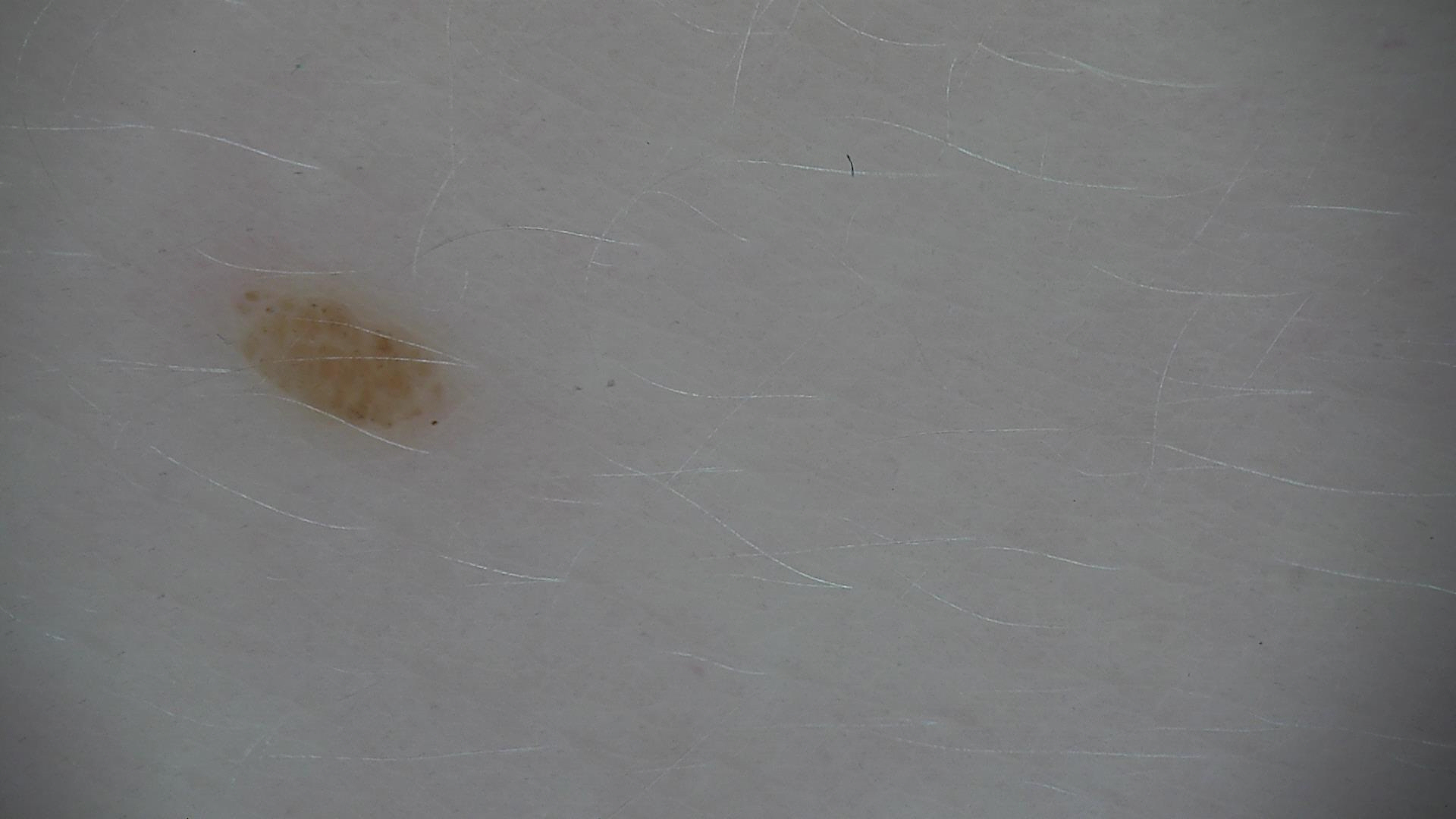category: banal | label: compound nevus (expert consensus).